Recorded as Fitzpatrick phototype I. The chart documents a previous melanoma. A dermoscopic photograph of a skin lesion — 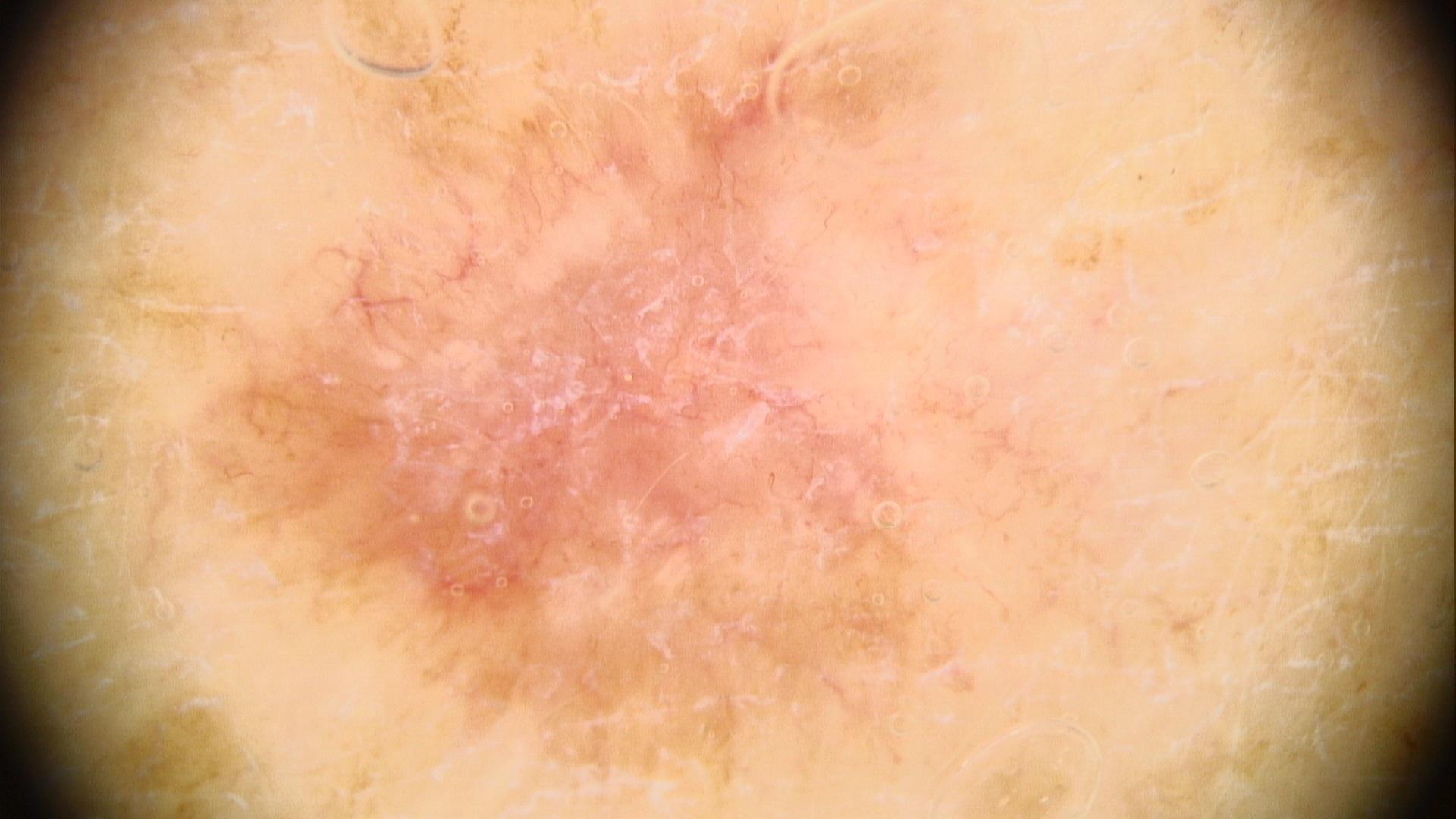pathology = Basal cell carcinoma (biopsy-proven).